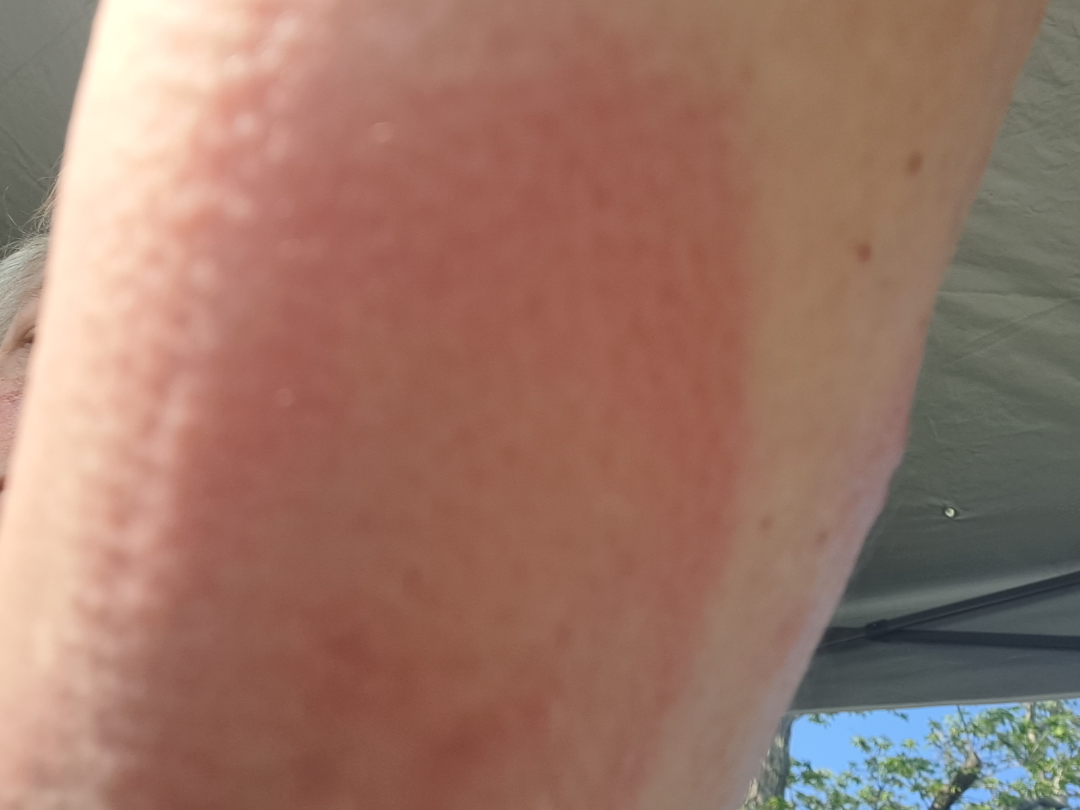{"assessment": "indeterminate", "shot_type": "close-up", "skin_tone": {"fitzpatrick": "I"}, "body_site": "arm", "patient_category": "a rash", "duration": "less than one week", "symptoms": ["burning", "pain"]}